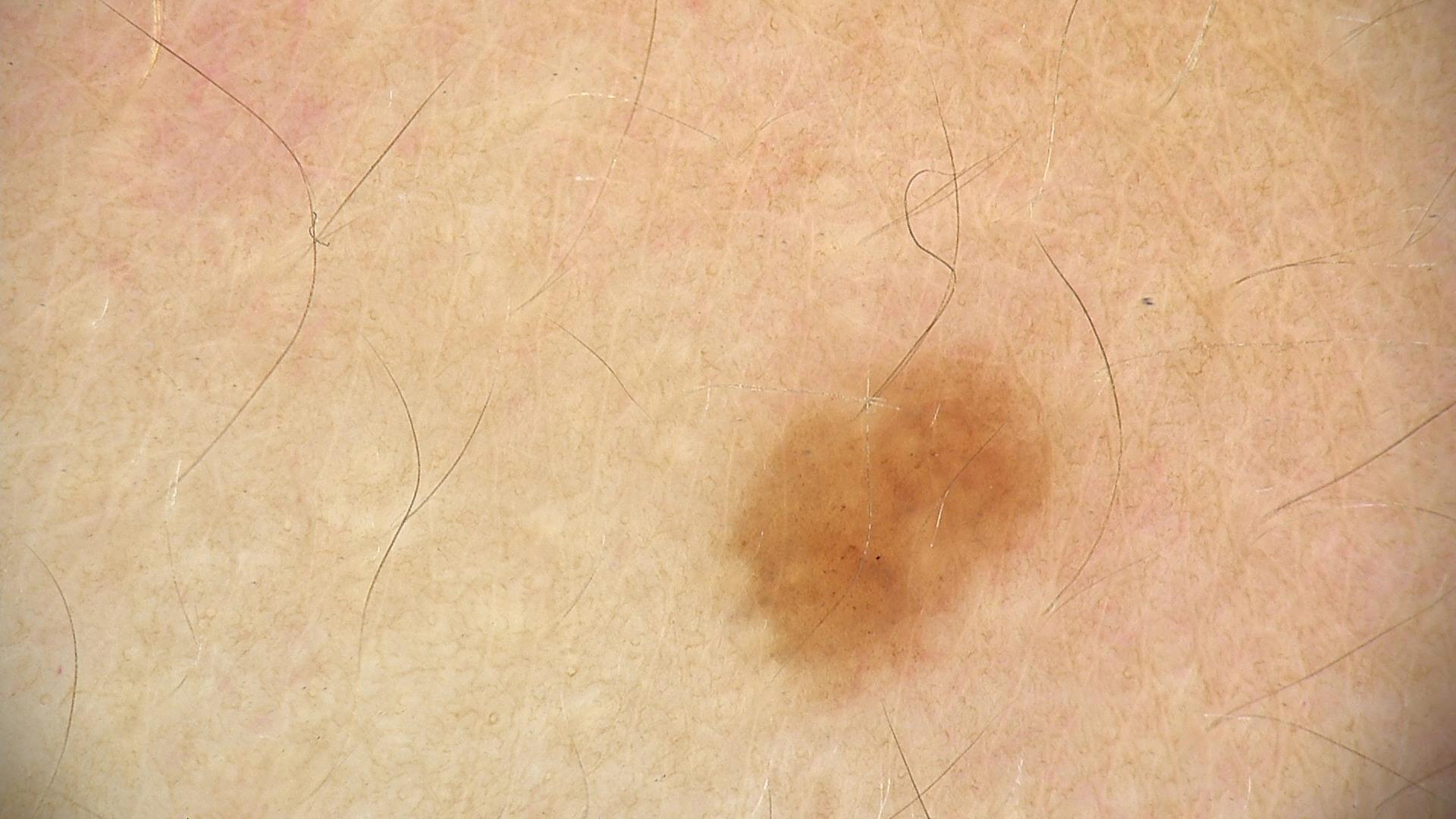Q: What is this lesion?
A: dysplastic junctional nevus (expert consensus)